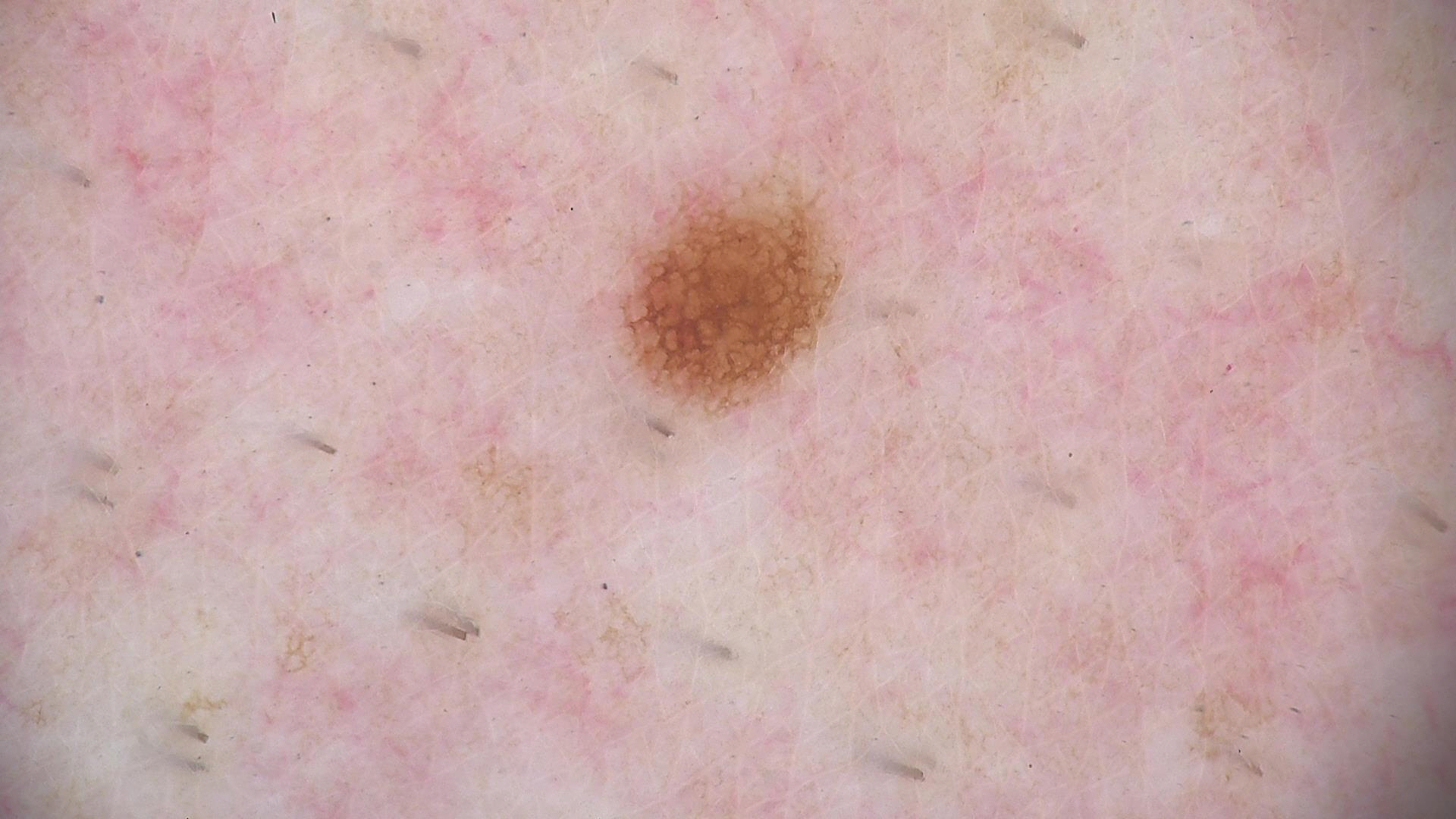<dermoscopy>
  <image>dermatoscopy</image>
  <diagnosis>
    <name>dysplastic junctional nevus</name>
    <code>jd</code>
    <malignancy>benign</malignancy>
    <super_class>melanocytic</super_class>
    <confirmation>expert consensus</confirmation>
  </diagnosis>
</dermoscopy>